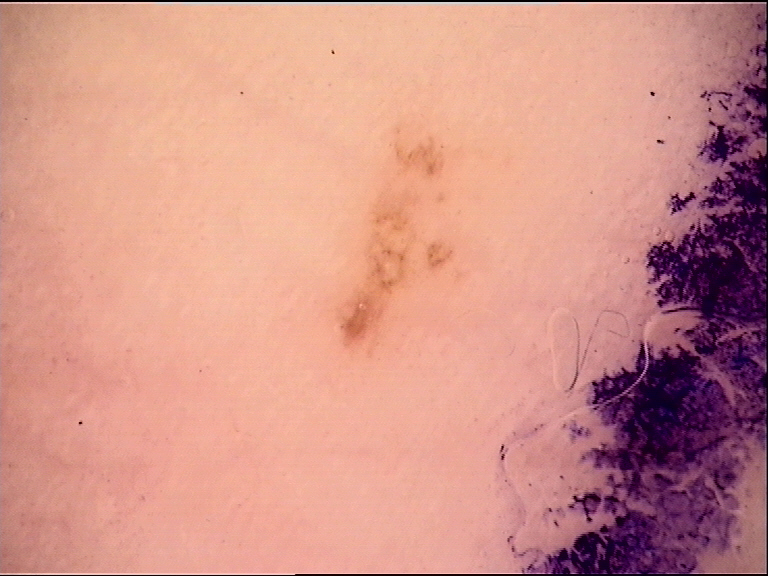| key | value |
|---|---|
| image type | dermatoscopy |
| diagnostic label | dysplastic junctional nevus (expert consensus) |